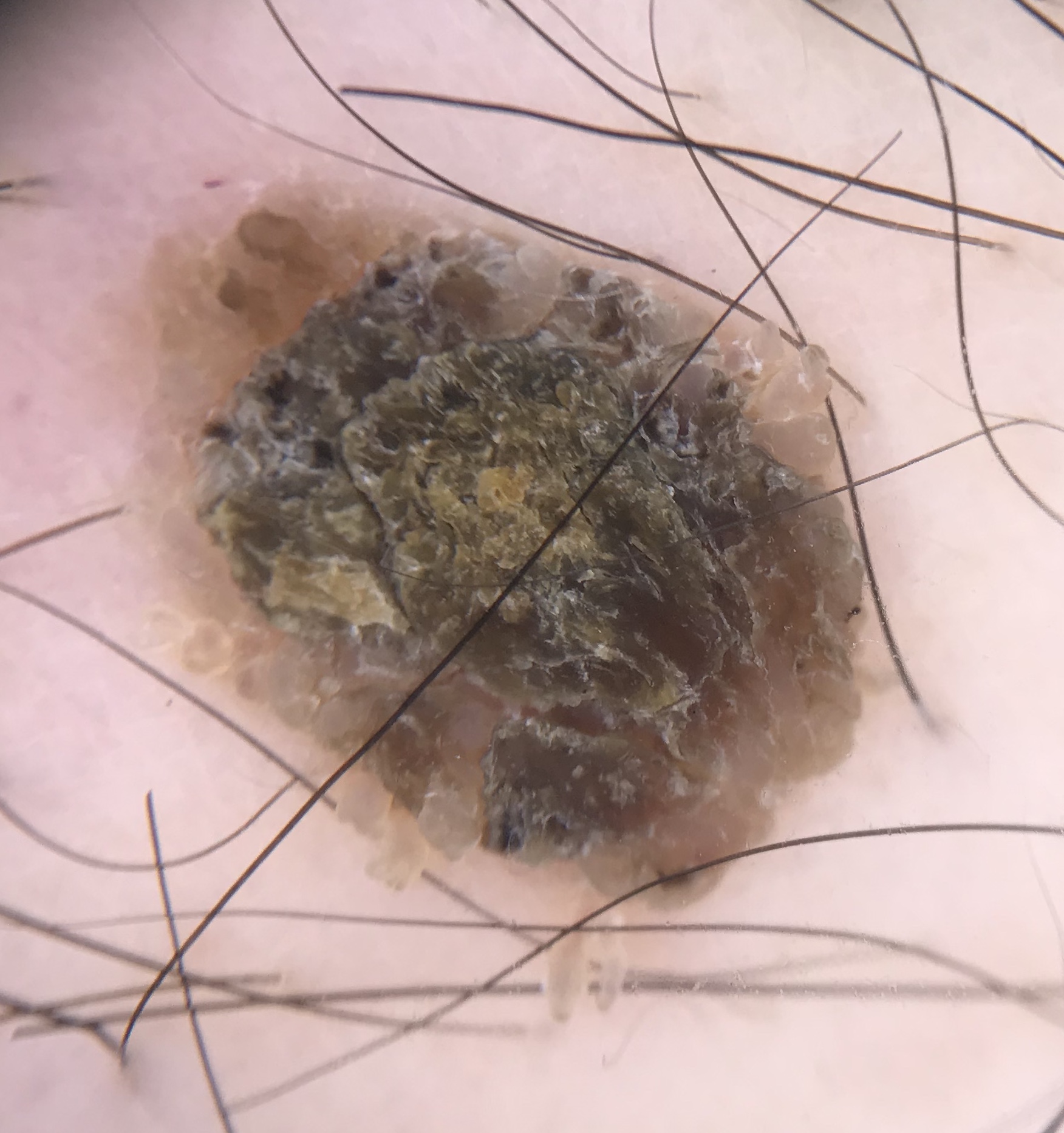modality=dermatoscopy | diagnosis=seborrheic keratosis (expert consensus).